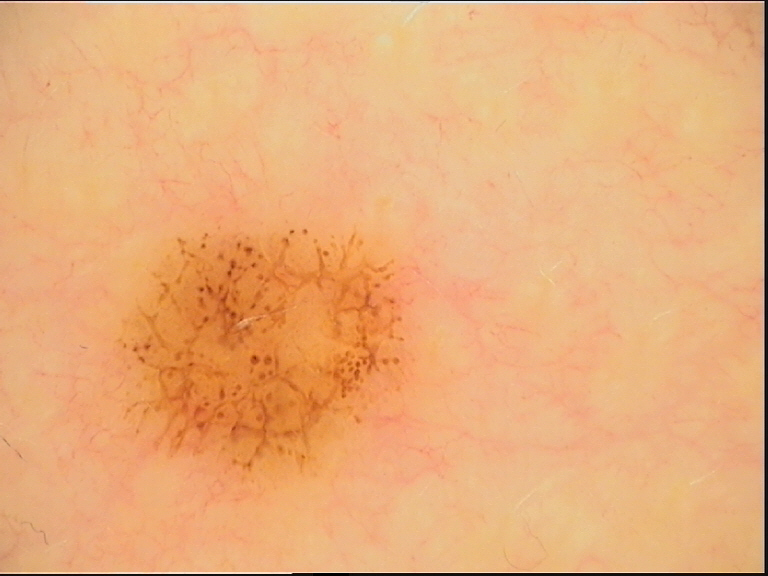Findings:
– diagnostic label · dysplastic junctional nevus (expert consensus)